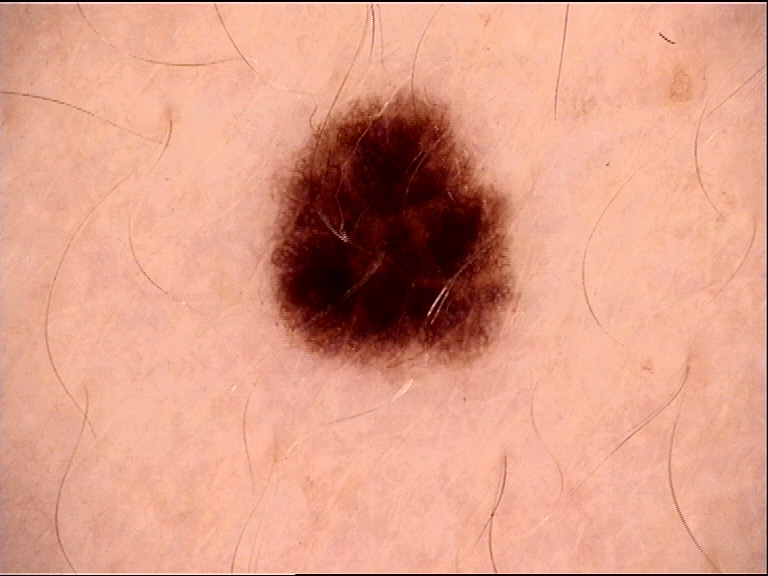Impression:
The diagnosis was a dysplastic junctional nevus.